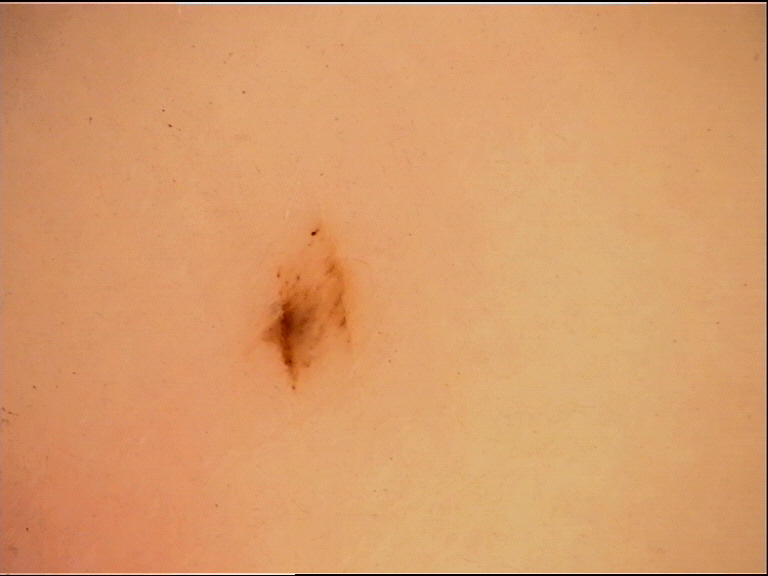A dermoscopy image of a single skin lesion.
The architecture is that of a banal lesion.
Consistent with an acral junctional nevus.